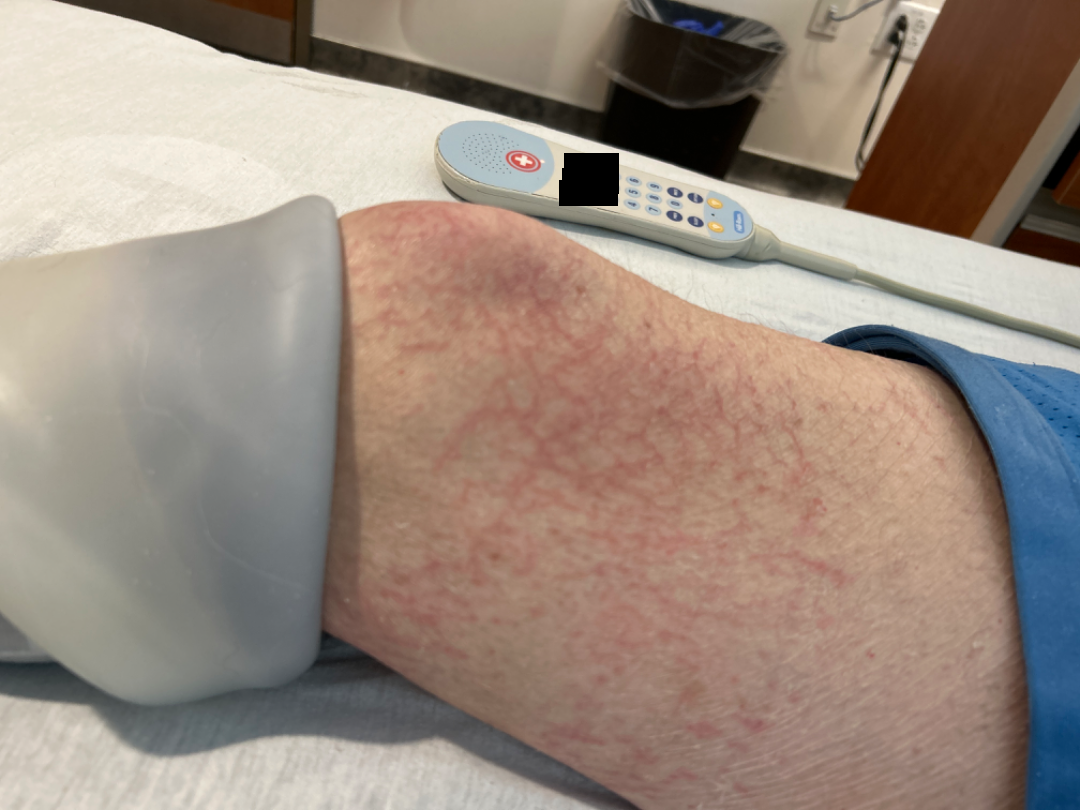view=at an angle
skin tone=lay reviewers estimated Monk Skin Tone 5 (US pool) or 3 (India pool)
differential diagnosis=Eczema (100%)